The affected area is the back of the hand, top or side of the foot, leg and arm. The photograph was taken at an angle — 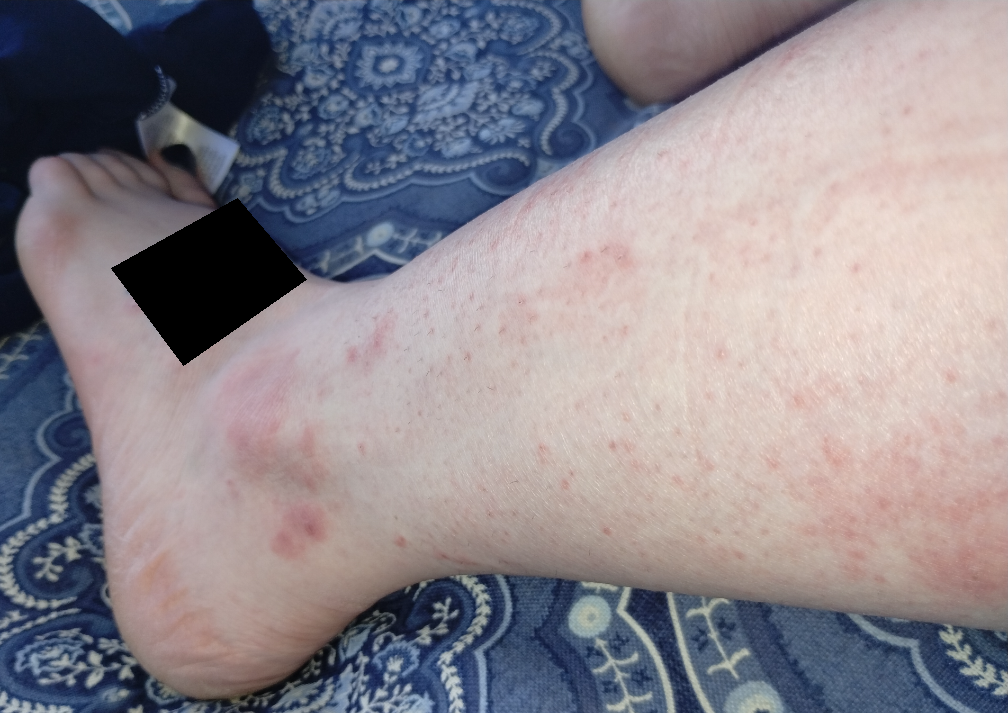| field | value |
|---|---|
| other reported symptoms | none reported |
| symptoms | itching |
| lesion texture | rough or flaky and raised or bumpy |
| patient's own categorization | a rash |
| symptom duration | less than one week |
| differential diagnosis | Folliculitis and Vasculitis of the skin were considered with similar weight |